A dermatoscopic image of a skin lesion: 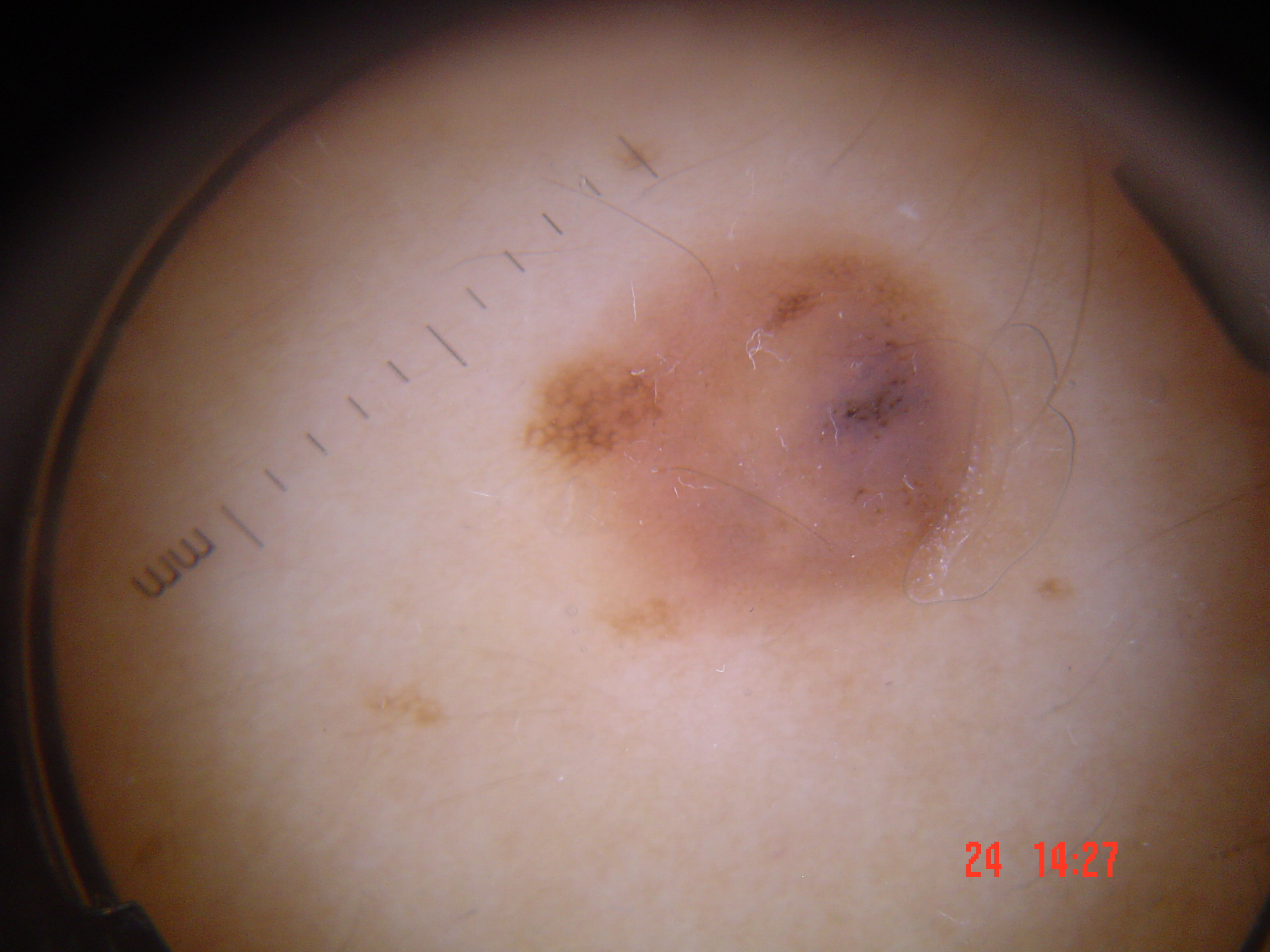Summary:
The architecture is that of a banal lesion.
Conclusion:
Classified as a congenital compound nevus.